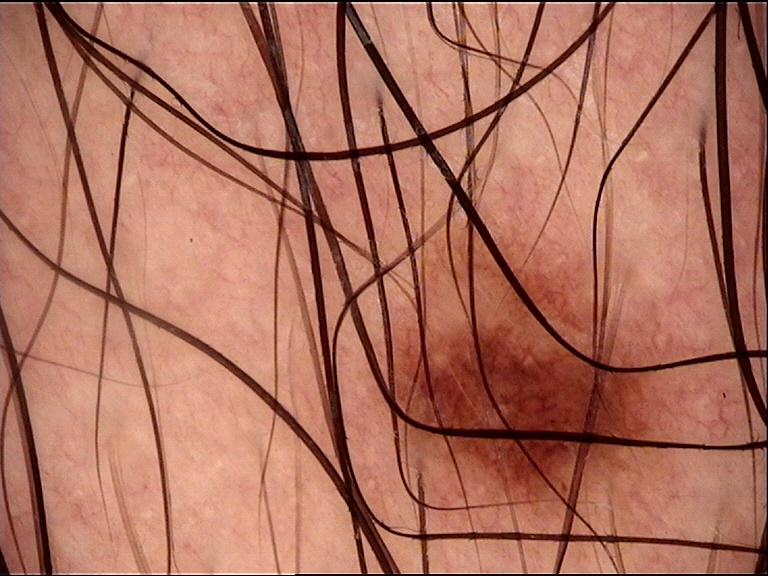Q: What is the imaging modality?
A: dermoscopy
Q: What is the diagnosis?
A: dysplastic junctional nevus (expert consensus)